A dermatoscopic image of a skin lesion.
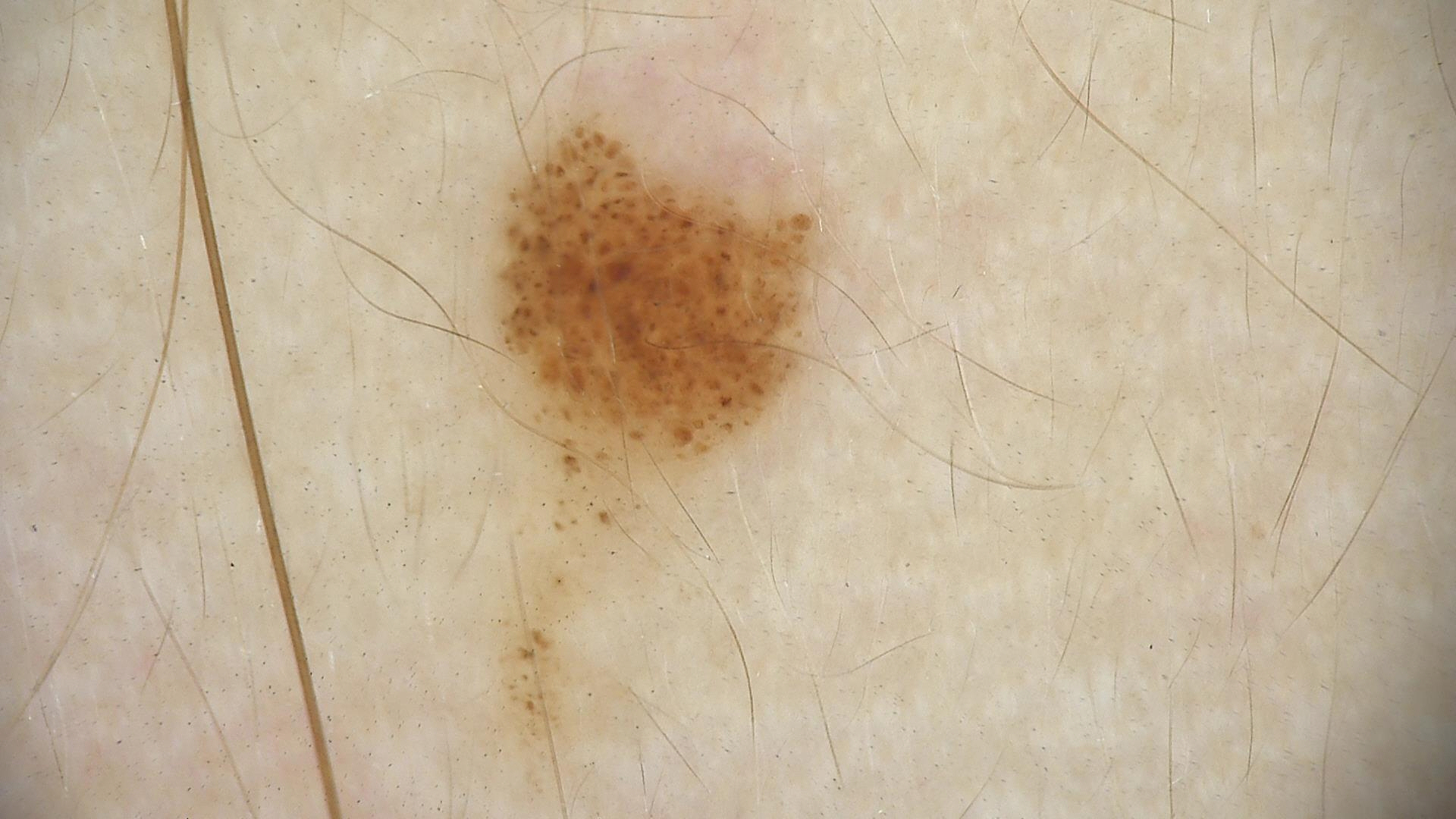assessment = dysplastic junctional nevus (expert consensus)